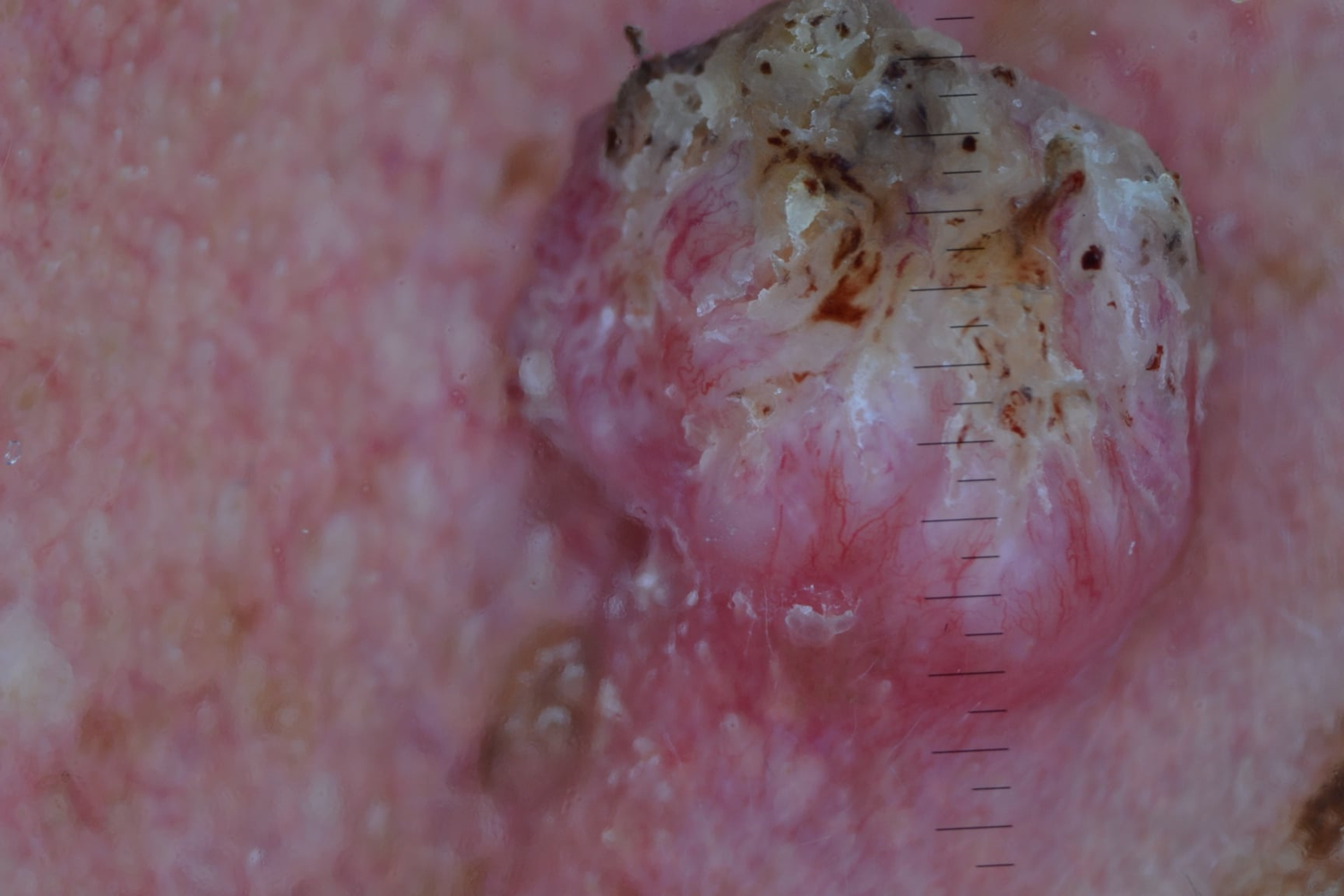The biopsy diagnosis was a keratinocytic lesion — a squamous cell carcinoma.